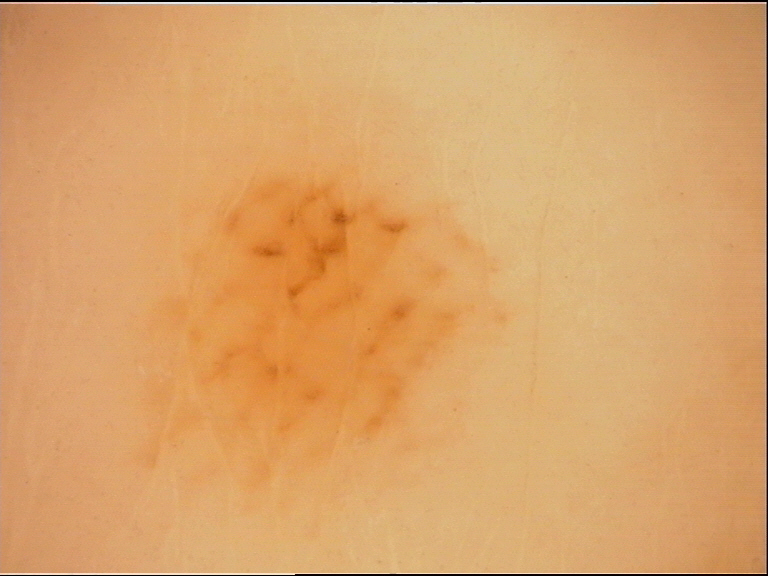Impression:
Consistent with a banal lesion — an acral junctional nevus.